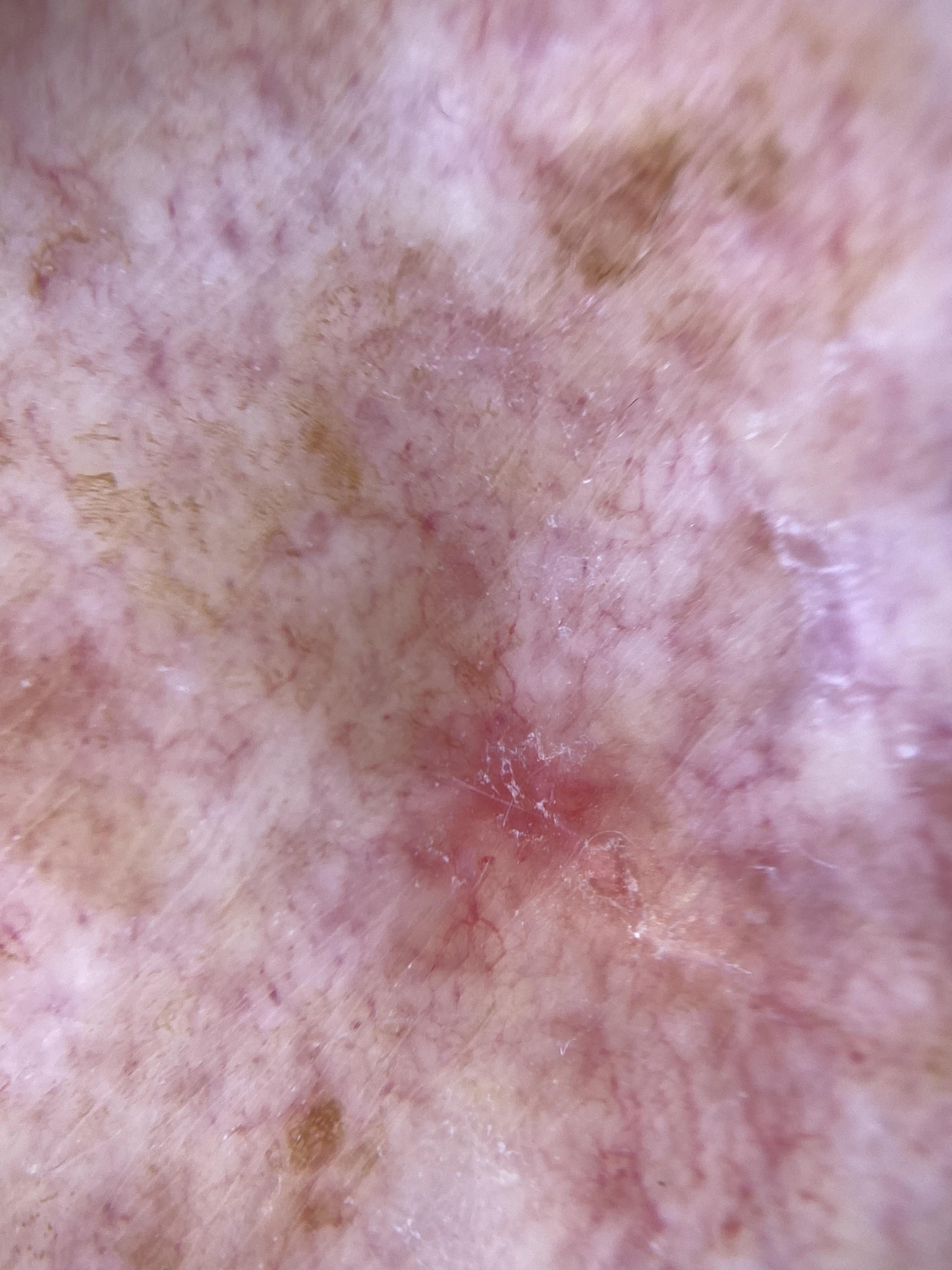Contact-polarized dermoscopy of a skin lesion. A female subject about 75 years old. Located on the trunk. On biopsy, the diagnosis was a squamous cell carcinoma.